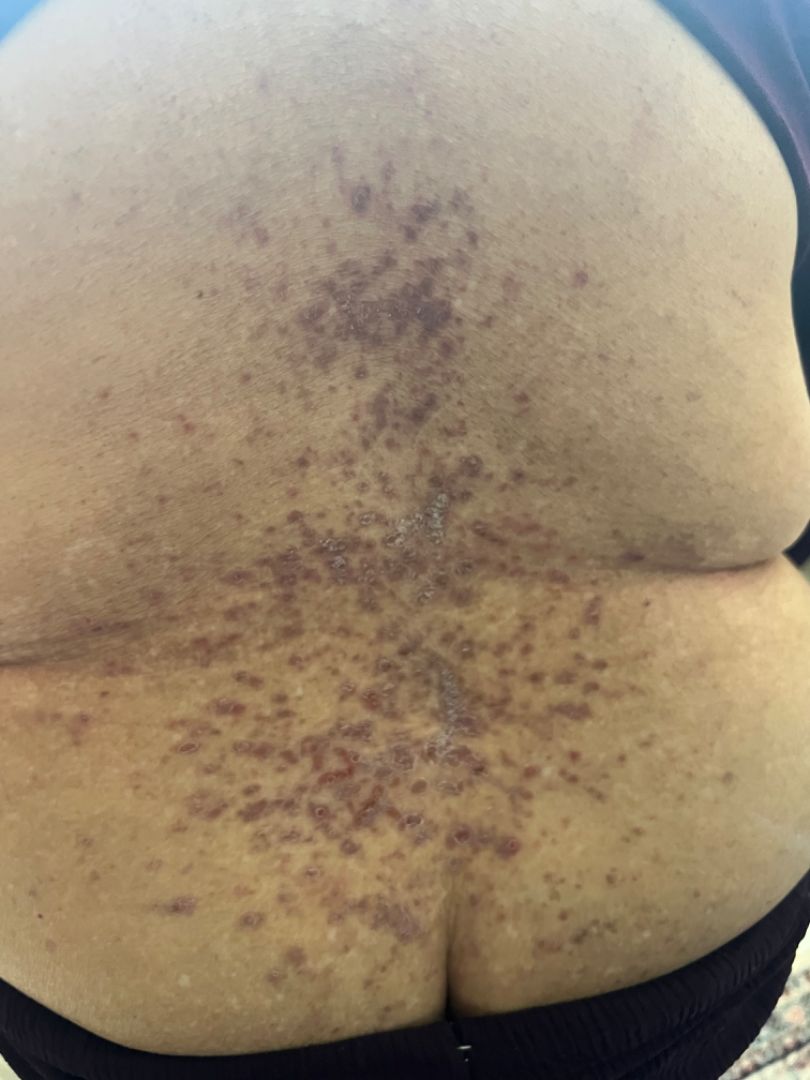The leading consideration is Lichen planus/lichenoid eruption; also on the differential is Drug Rash.